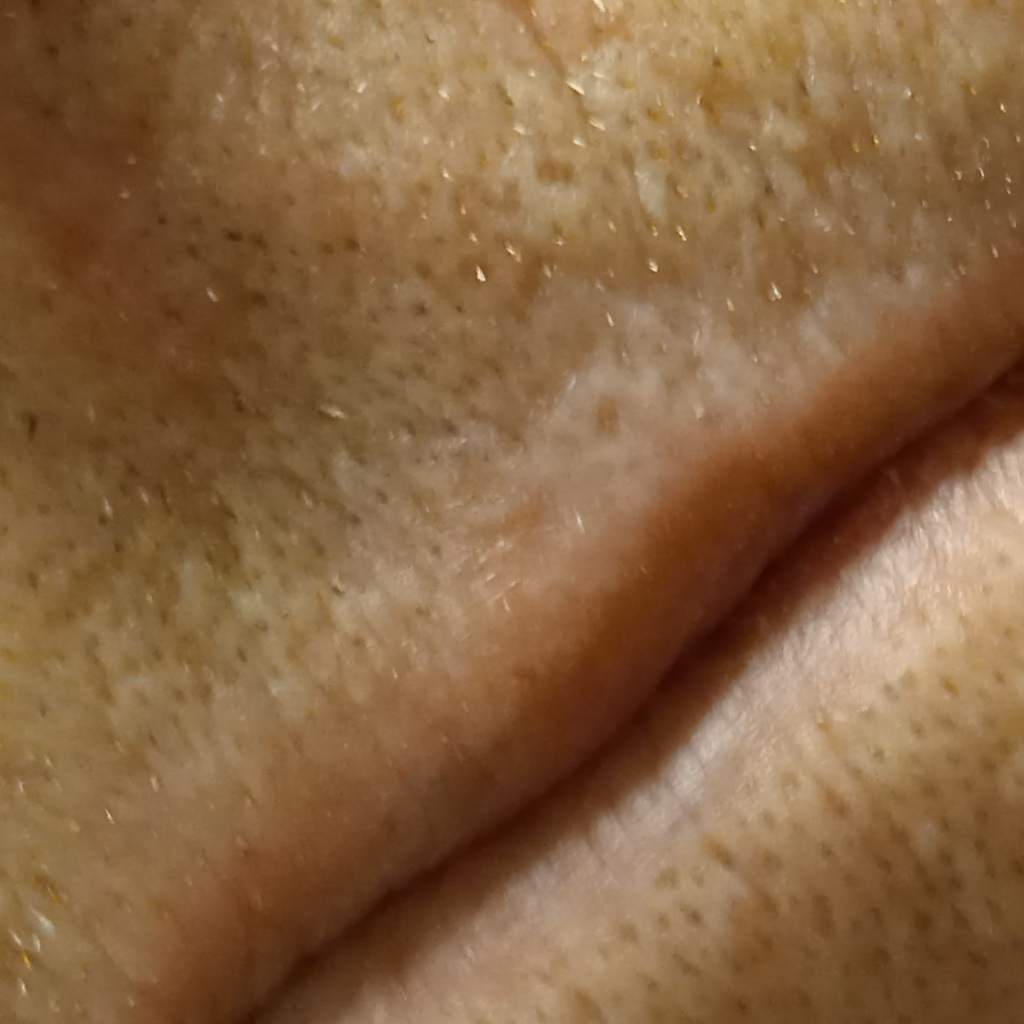sun reaction: skin reddens with sun exposure; patient: male, aged 77; referral: research study (no referral diagnosis); image: clinical photograph; risk factors: a personal history of skin cancer, a personal history of cancer; anatomic site: the face; size: 6.4 mm; assessment: actinic keratosis (dermatologist consensus).